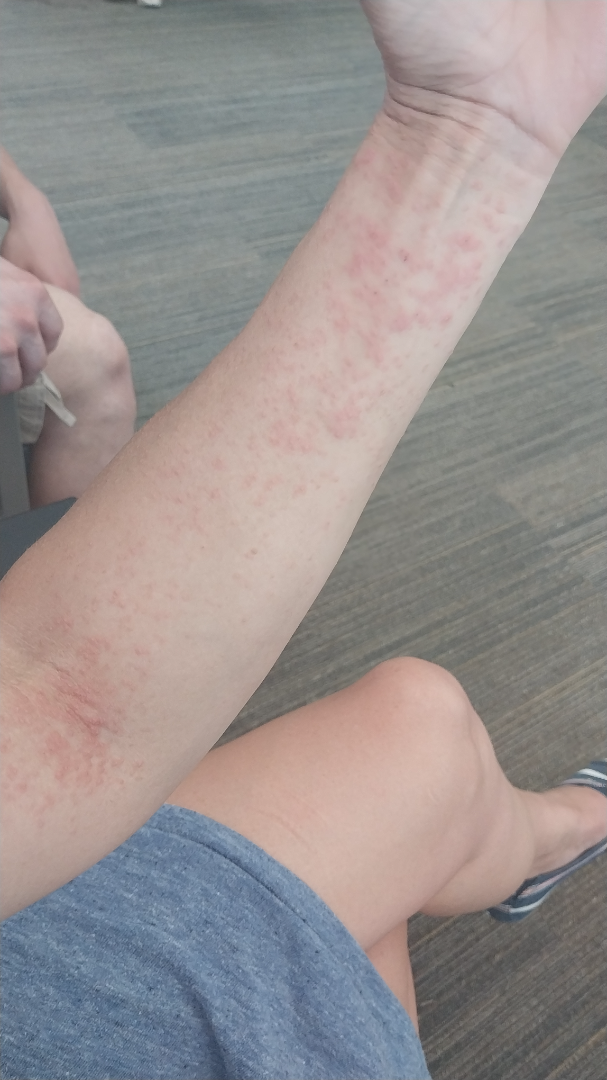Fitzpatrick II.
The lesion is associated with darkening, enlargement, burning, itching and bothersome appearance.
The contributor is female.
An image taken at a distance.
The patient described the issue as a rash.
Texture is reported as rough or flaky and raised or bumpy.
The condition has been present for less than one week.
The lesion involves the arm.
The differential includes Contact dermatitis and Eczema, with no clear leading consideration; also consider Dermatitis herpetiformis.